The patient says their skin tans without first burning. A dermoscopy image of a skin lesion. Few moles overall by the patient's own estimate. By self-report, a personal history of skin cancer, no prior organ transplant, and no immunosuppression — 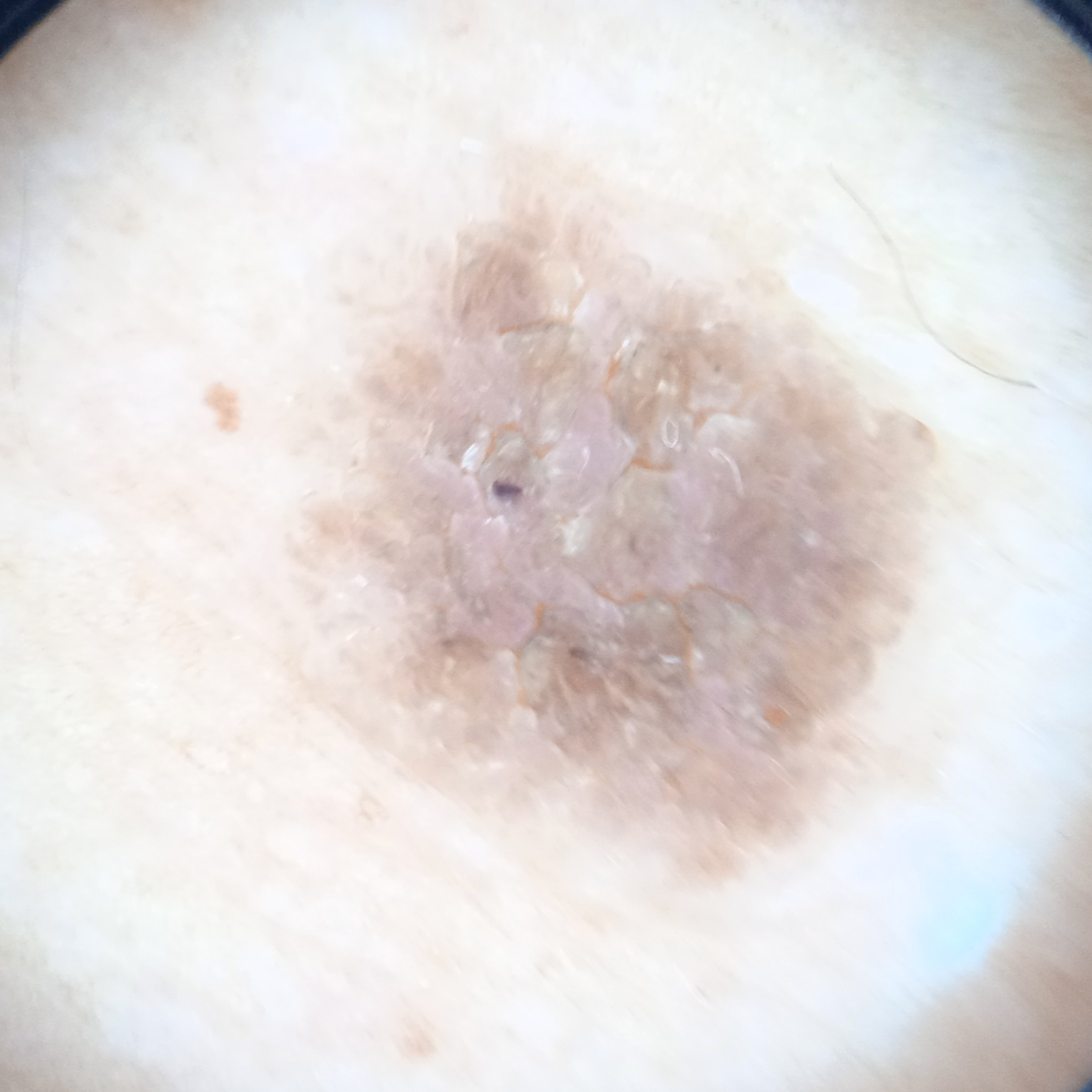Case summary:
Located on the back. The lesion measures approximately 8.9 mm.
Conclusion:
The four-dermatologist consensus diagnosis was a seborrheic keratosis; all four reviewers agreed; diagnostic confidence was good.